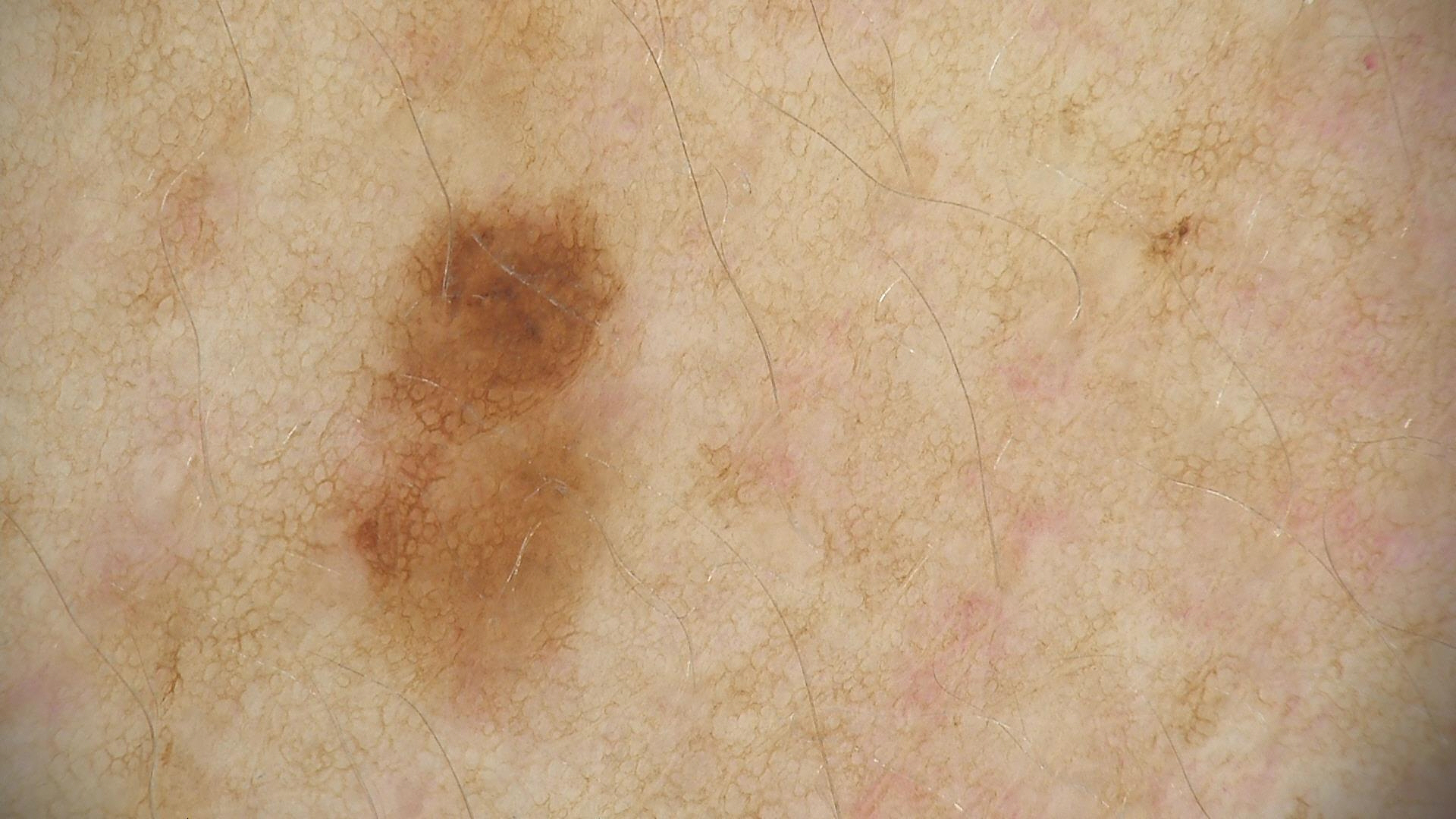  image: dermatoscopy
  diagnosis:
    name: dysplastic junctional nevus
    code: jd
    malignancy: benign
    super_class: melanocytic
    confirmation: expert consensus